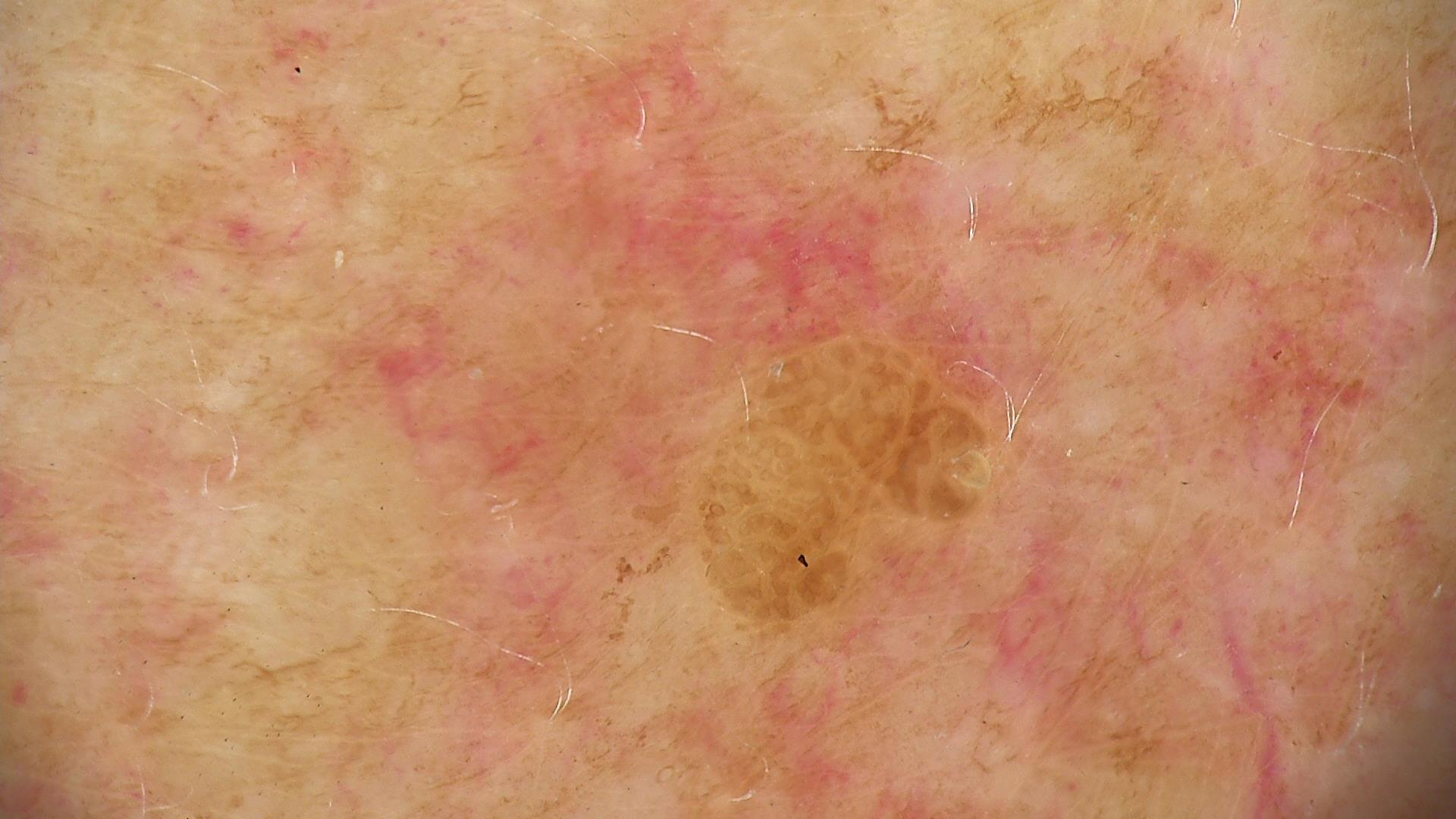class: seborrheic keratosis (expert consensus).